The photograph is a close-up of the affected area; the lesion involves the back of the hand — 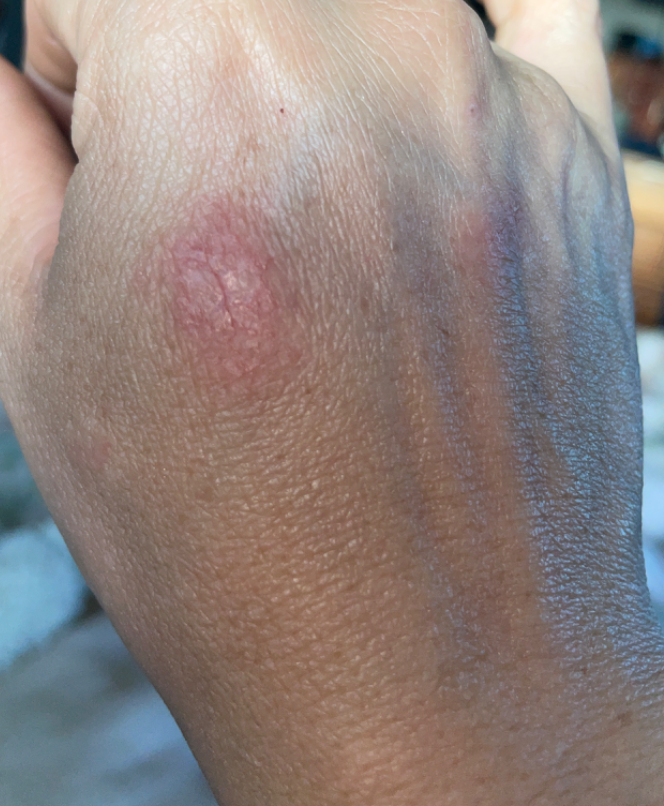systemic symptoms: fatigue and joint pain
duration: less than one week
reported symptoms: itching, burning and pain
surface texture: rough or flaky
clinical impression: the differential, in no particular order, includes Prurigo nodularis and Eczema; less likely is Insect Bite; a remote consideration is Lichen Simplex Chronicus; less probable is Keratosis